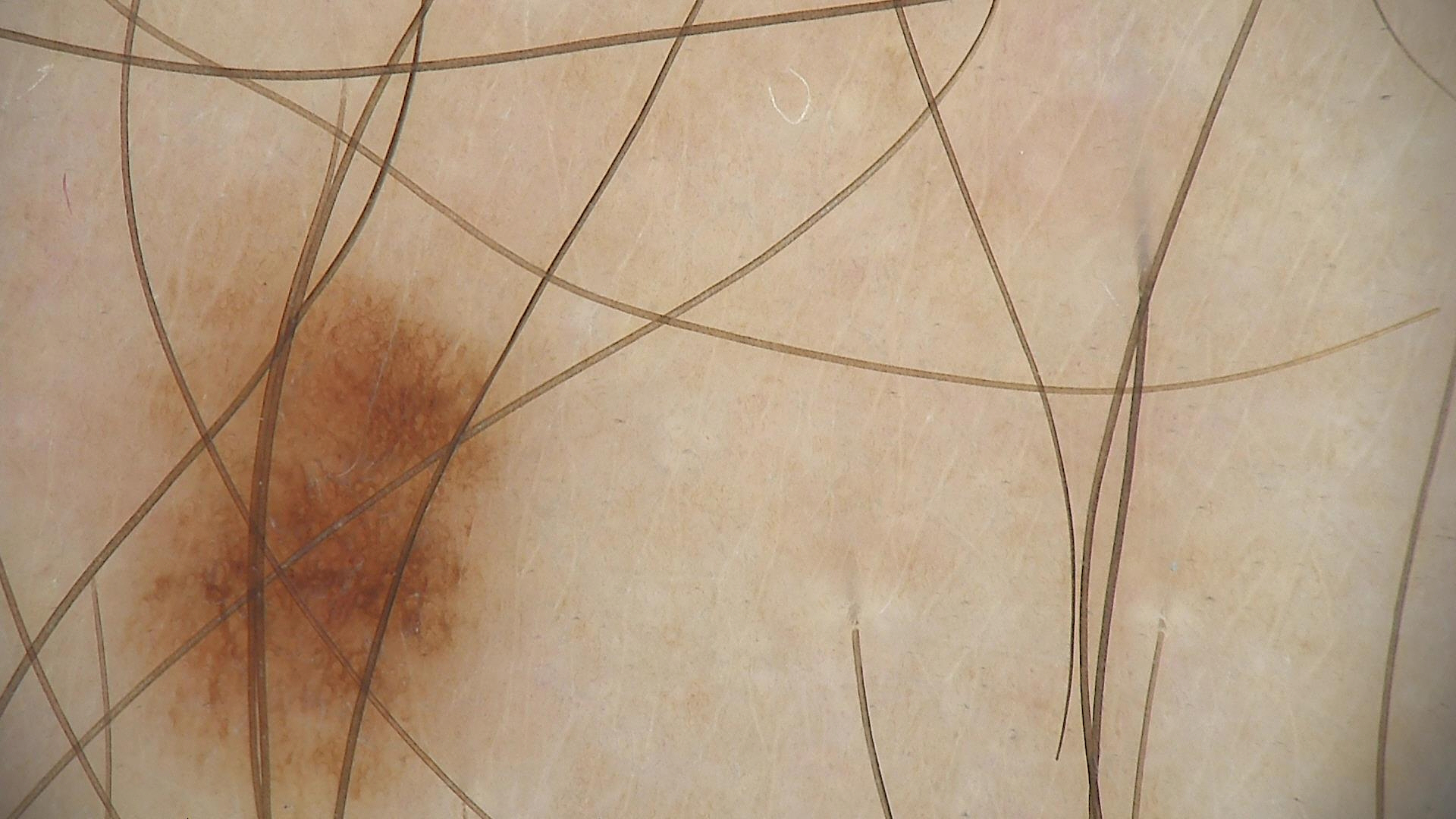Q: What kind of image is this?
A: dermoscopy
Q: What is the diagnosis?
A: dysplastic junctional nevus (expert consensus)